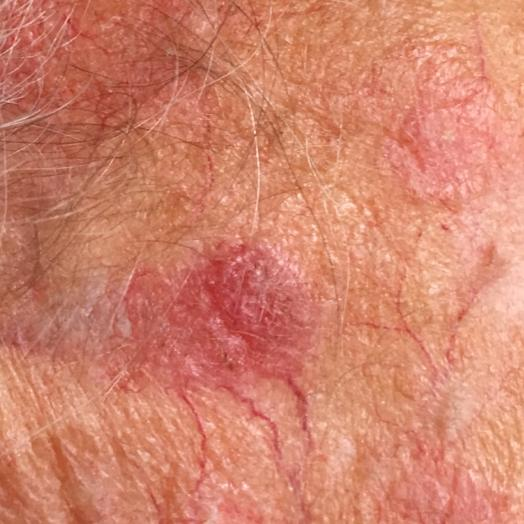Q: What was the clinical impression?
A: actinic keratosis (clinical consensus)